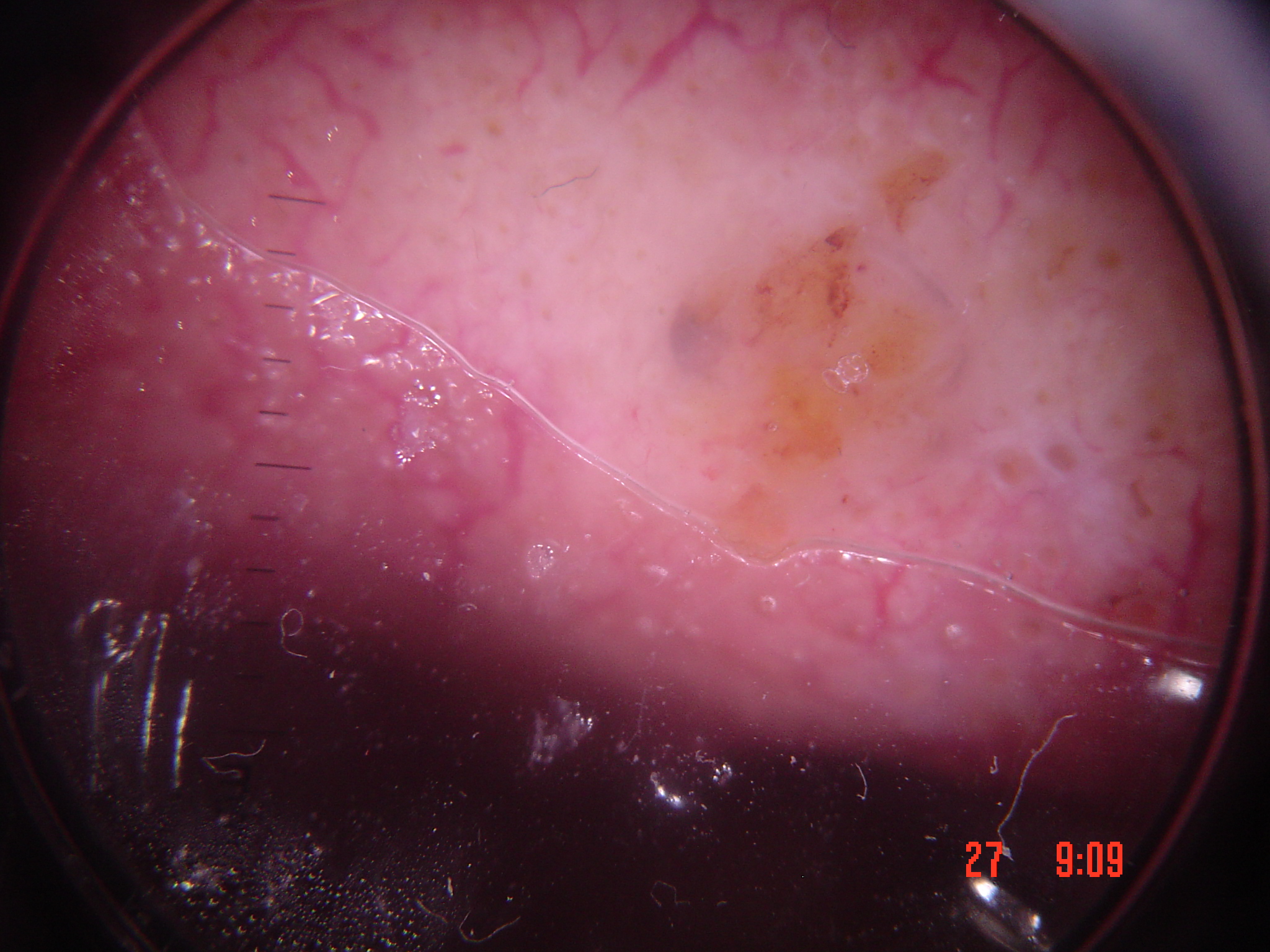Dermoscopy of a skin lesion.
The morphology is that of a keratinocytic lesion.
Histopathologically confirmed as a squamous cell carcinoma.